The subject is a male aged 30–39 · a close-up photograph · the affected area is the leg · reported duration is about one day · skin tone: Fitzpatrick skin type III; lay reviewers estimated MST 2 or 3 (two reviewer pools) · the patient indicates pain, enlargement and bothersome appearance · the patient described the issue as a rash · the patient indicates associated chills and joint pain · the patient indicates the lesion is rough or flaky.
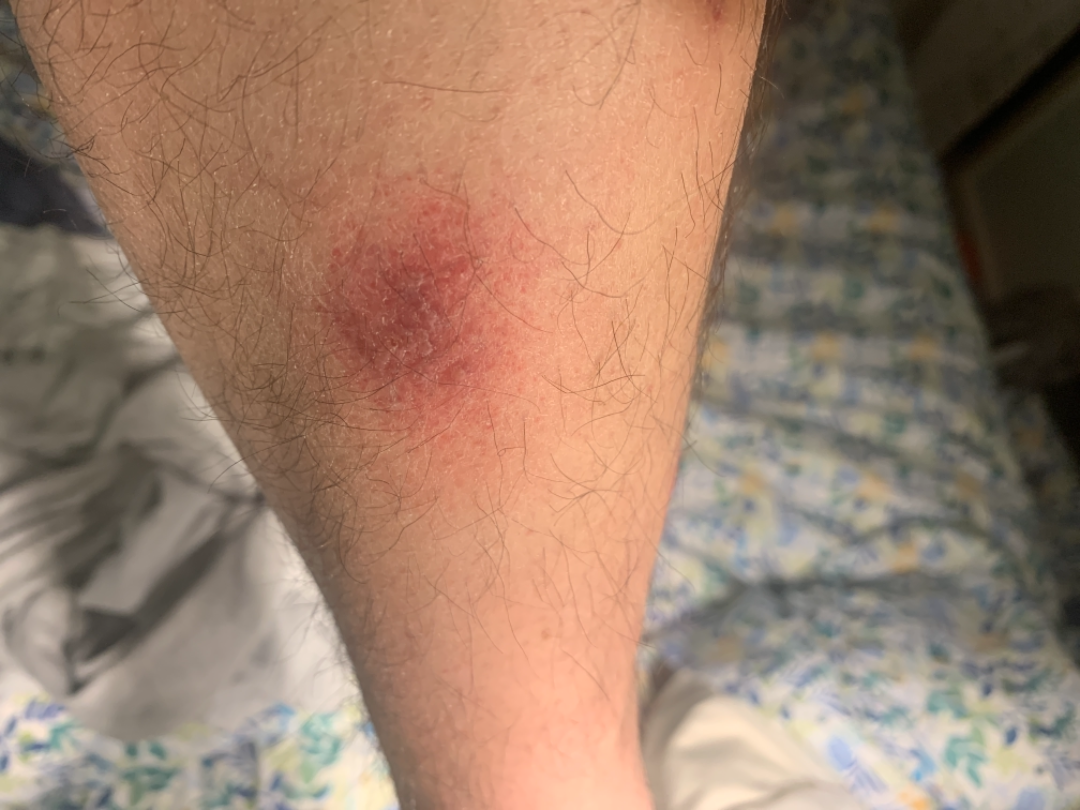On teledermatology review: Eczema (leading); Stasis Dermatitis (possible); Pigmented purpuric eruption (possible).